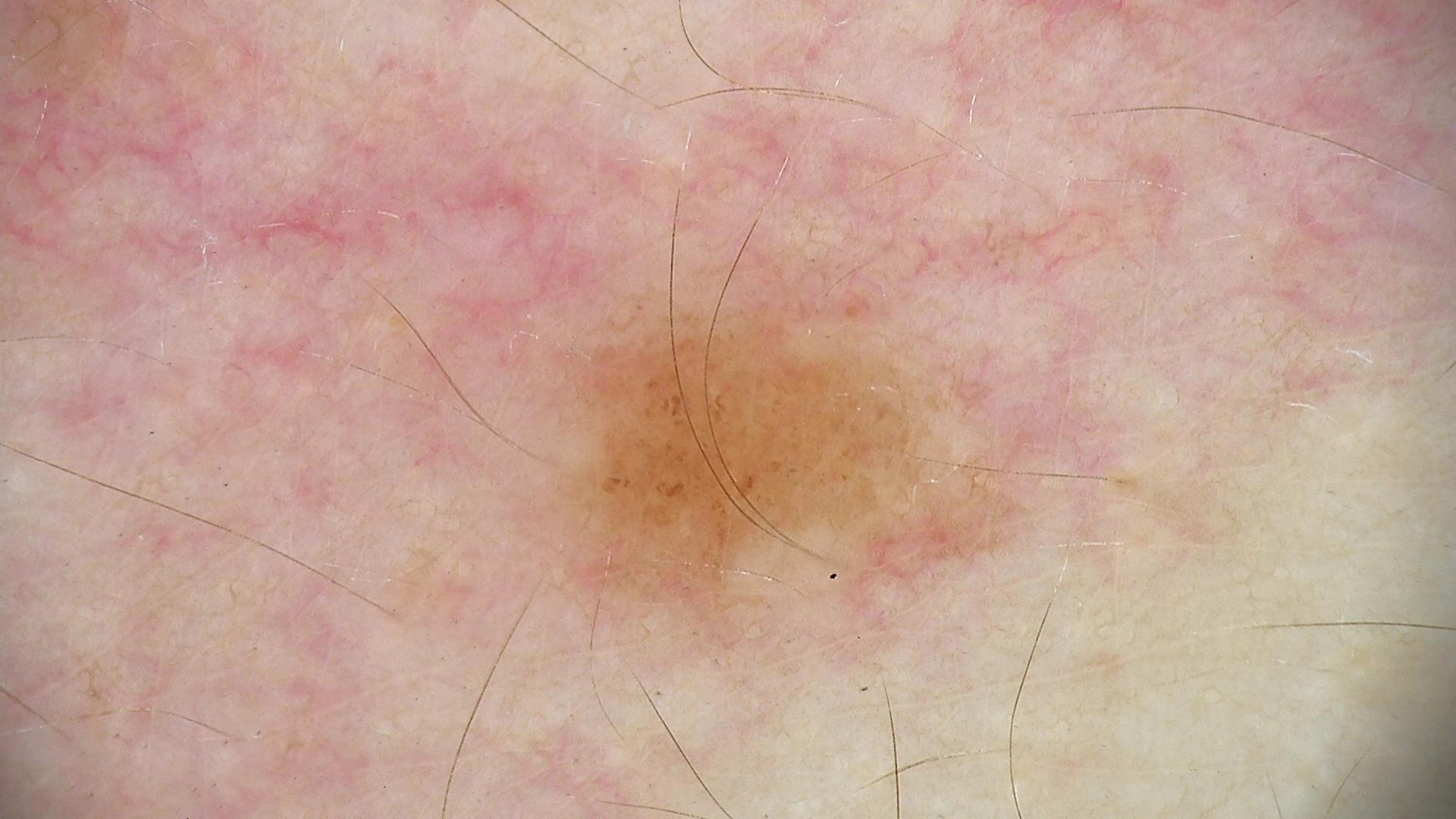A skin lesion imaged with a dermatoscope. The diagnosis was a dysplastic junctional nevus.